An image taken at a distance. The patient indicates the condition has been present for less than one week. The lesion is described as rough or flaky. Fitzpatrick skin type III; lay reviewers estimated Monk Skin Tone 3 or 6. Self-categorized by the patient as a rash. The contributor is 18–29, female. Symptoms reported: itching. The leg and arm are involved — 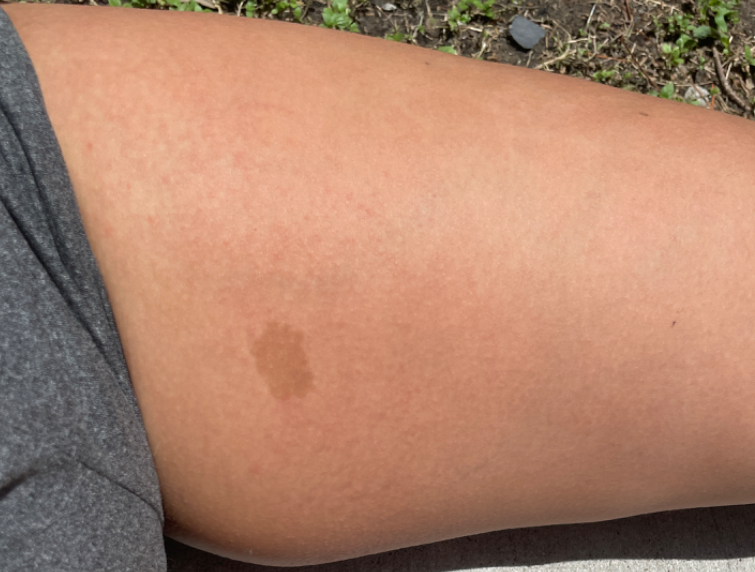Review:
The reviewing dermatologist did not identify a discernible skin condition.